A dermoscopic image of a skin lesion. A female subject 50 years of age. Imaged for a research study, with no referral diagnosis recorded:
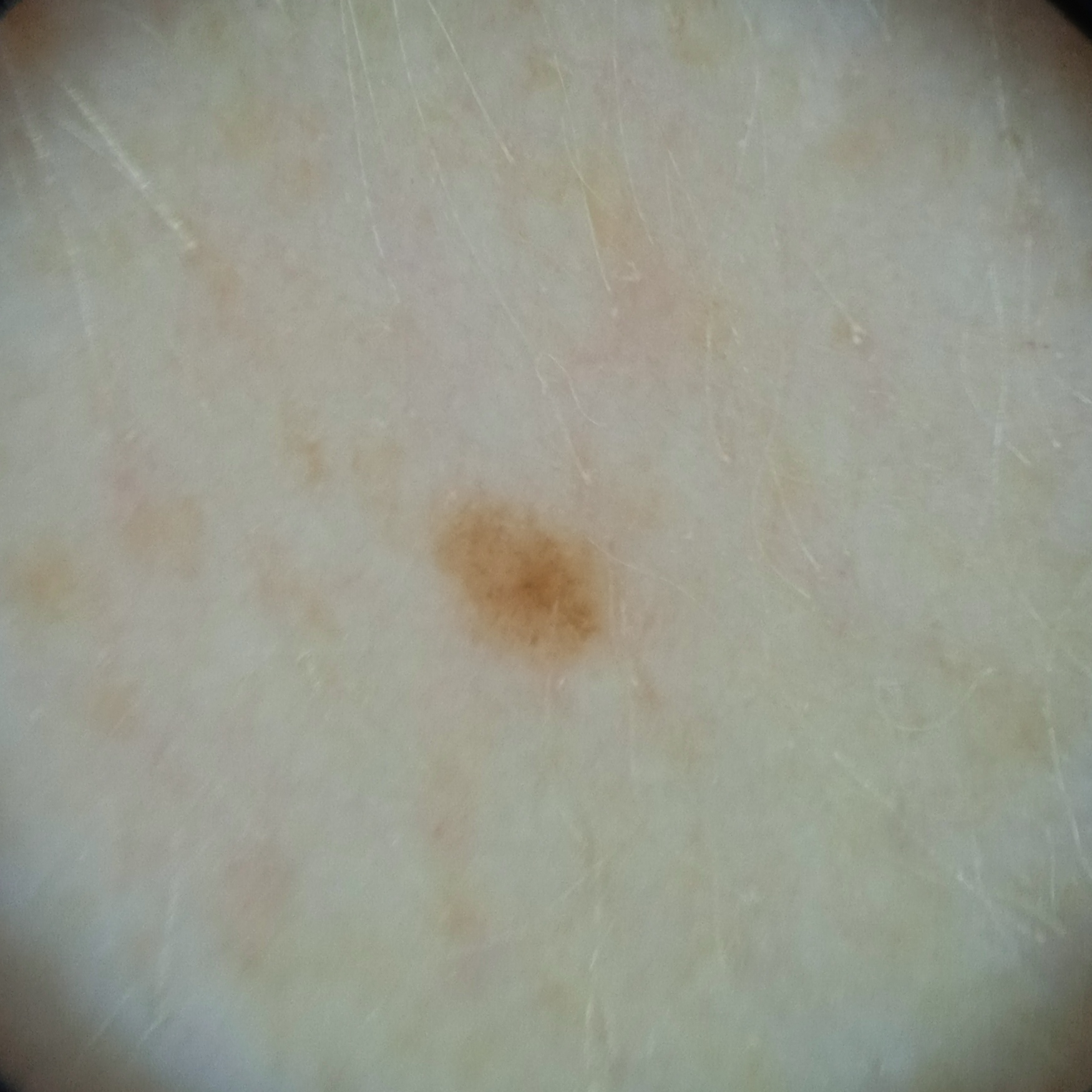The lesion is on an arm.
The lesion measures approximately 2 mm.
Reviewed by four dermatologists, the consensus diagnosis was a melanocytic nevus; agreement among the reviewers was unanimous; the reviewers were moderately confident.